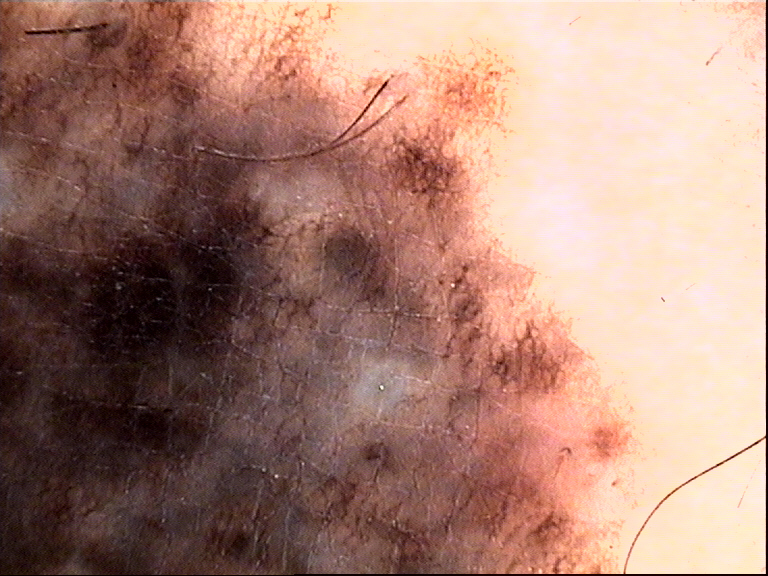image: dermoscopy
diagnosis: congenital compound nevus (expert consensus)